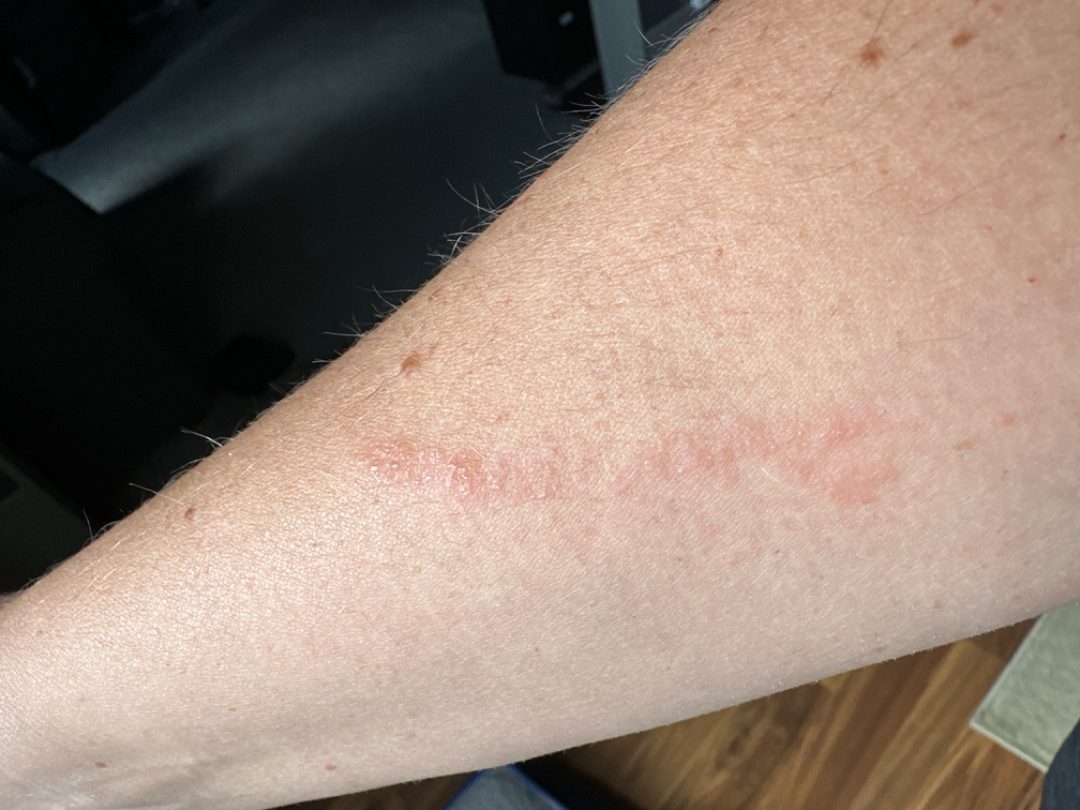assessment: unable to determine | site: arm | shot type: close-up | subject: female, age 30–39.